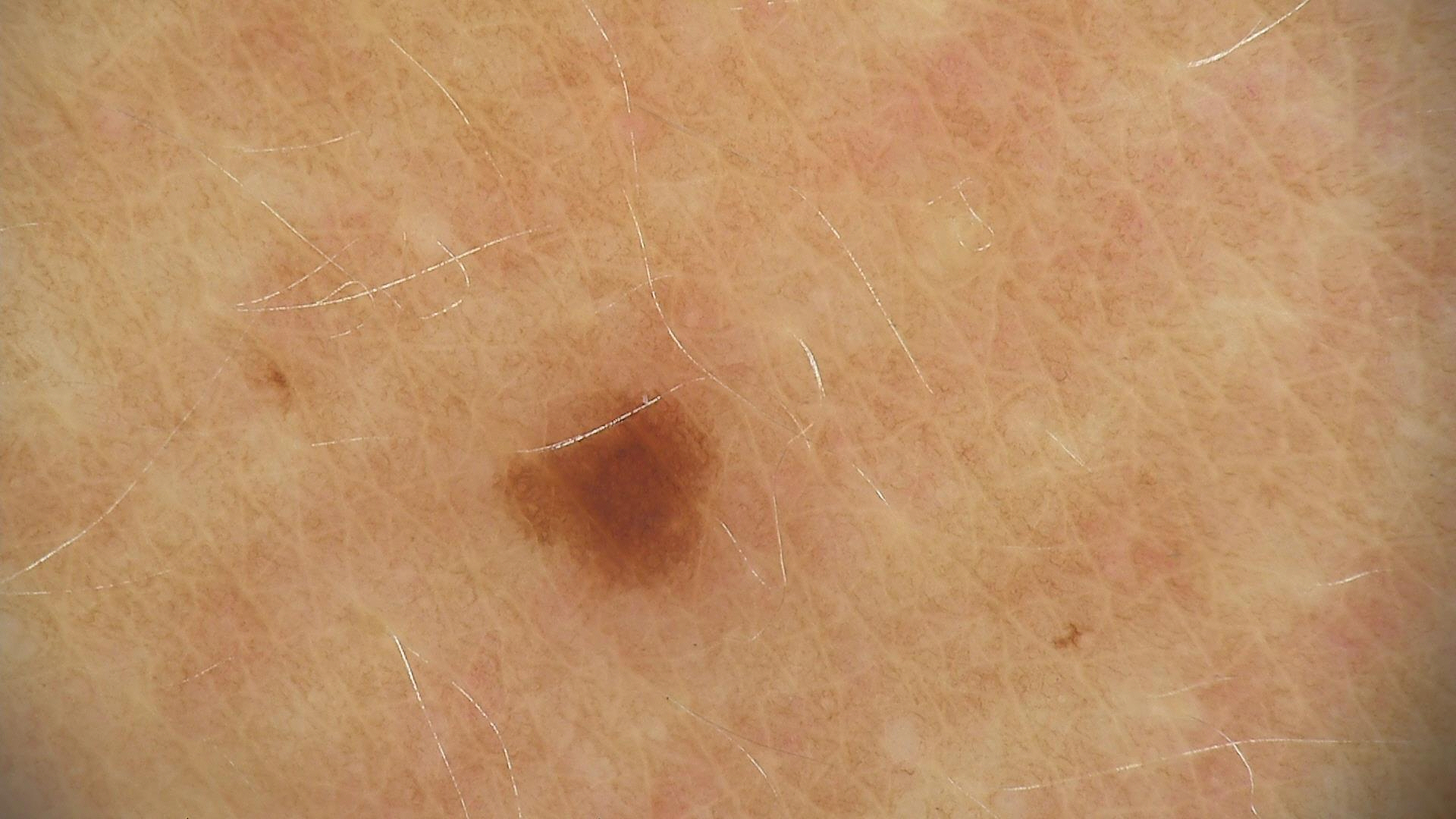Labeled as a dysplastic junctional nevus.